The affected area is the front of the torso, arm and back of the torso; the photo was captured at a distance; male contributor, age 40–49:
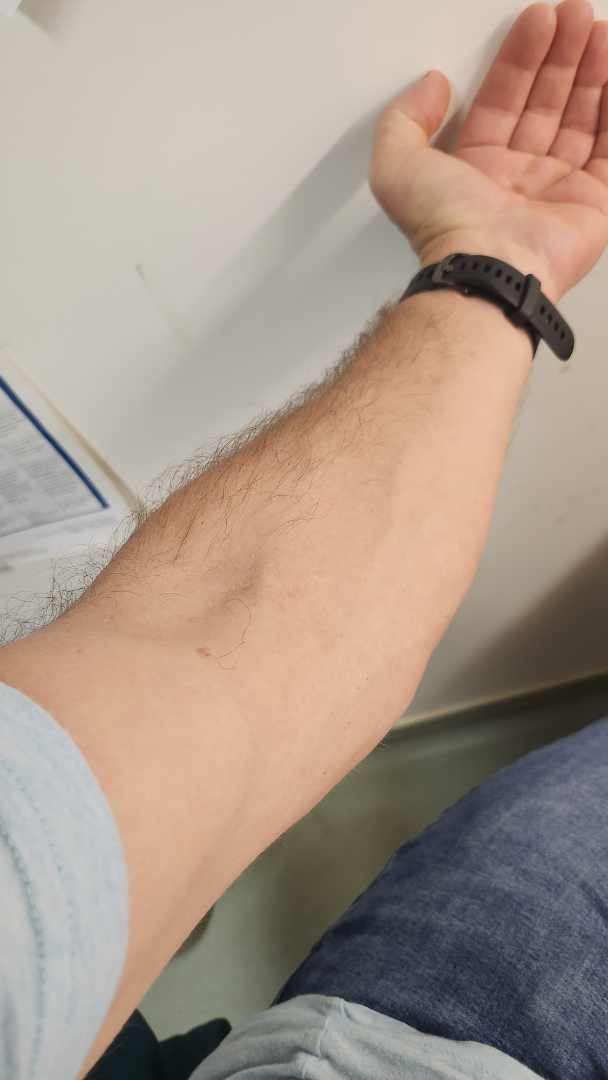Findings:
The case was indeterminate on photographic review.
Background:
The patient indicates the condition has been present for less than one week. The patient indicates the lesion is raised or bumpy. The patient described the issue as a rash.